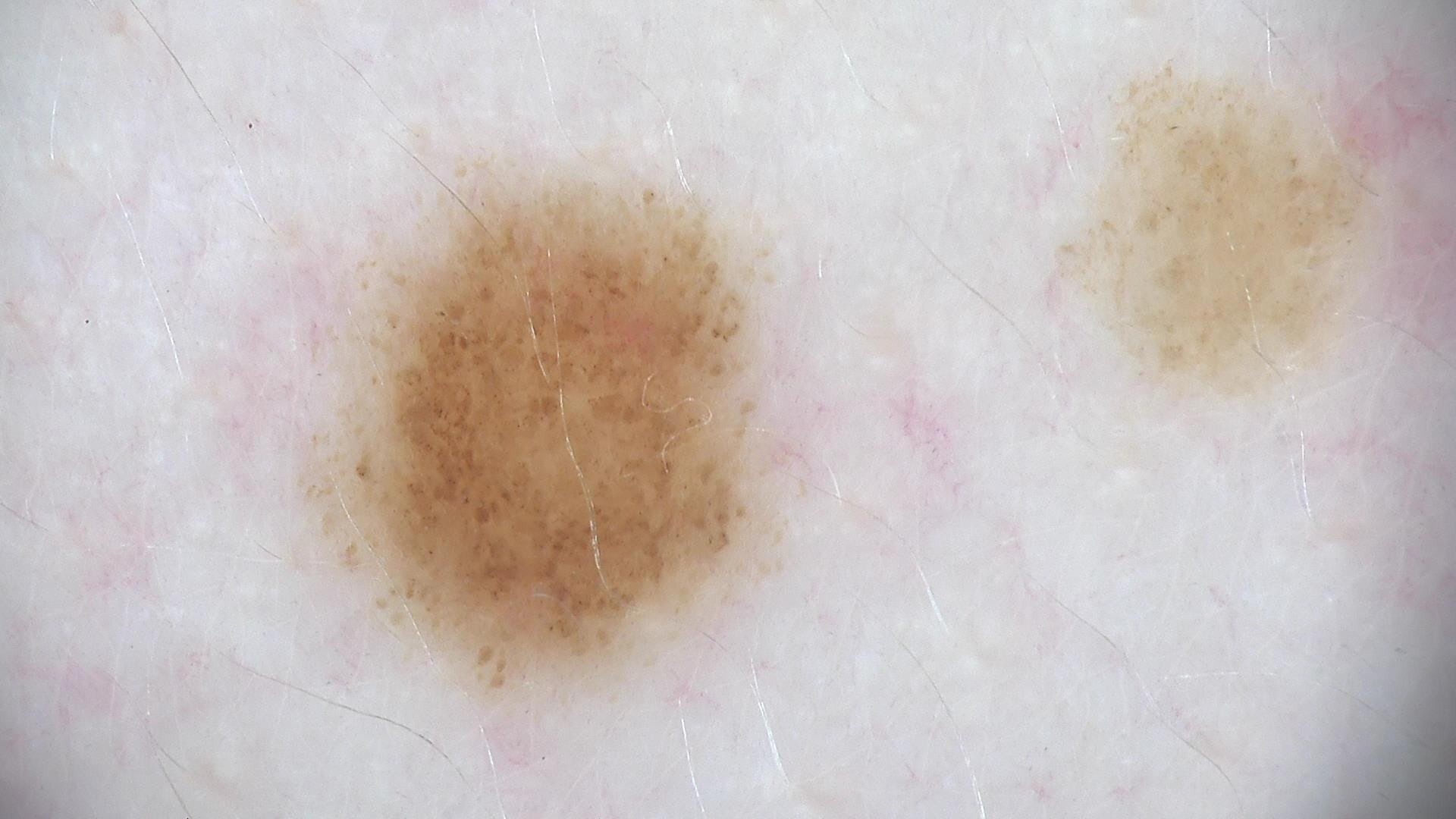A dermoscopic close-up of a skin lesion.
The architecture is that of a banal lesion.
Consistent with a compound nevus.